The lesion involves the arm and back of the hand. Present for more than one year. The subject is a female aged 18–29. The patient described the issue as a pigmentary problem. This image was taken at a distance:
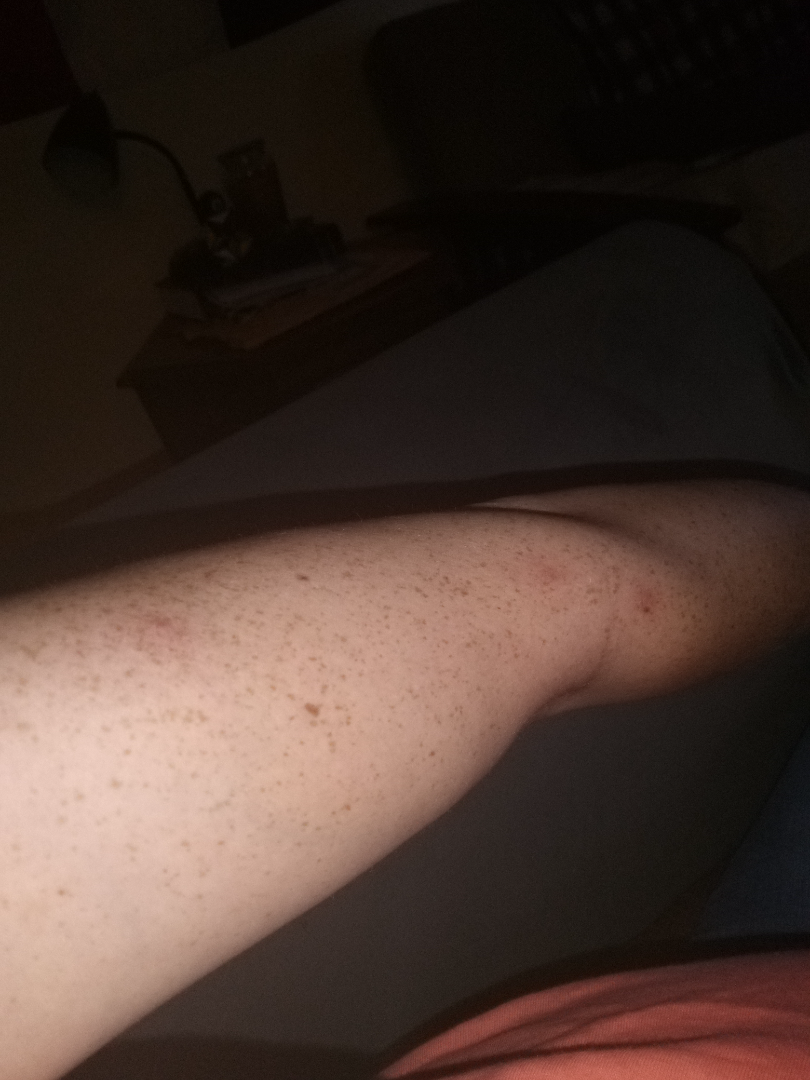Case summary:
– clinical impression · Folliculitis (0.50); Insect Bite (0.50)